The lesion is described as raised or bumpy; the subject is a male aged 30–39; the lesion involves the arm; the patient considered this a rash; the photo was captured at an angle; present for one to three months; the contributor reports itching:
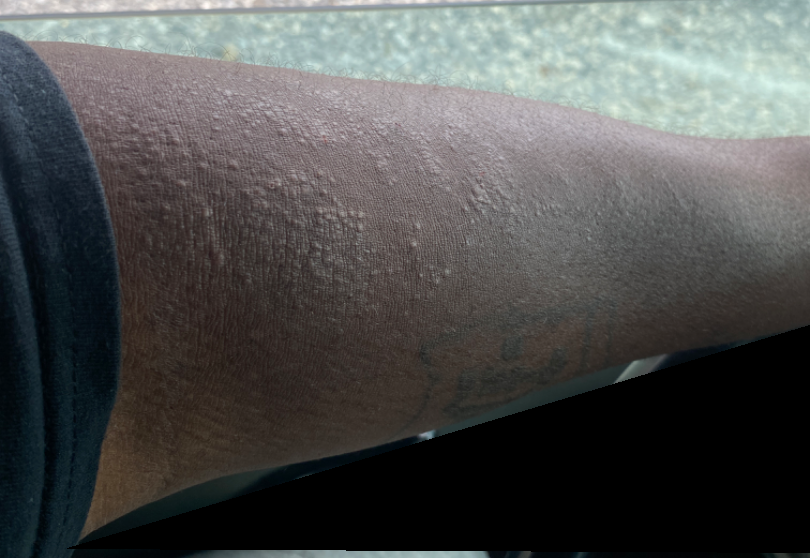On independent review by the dermatologists, the differential, in no particular order, includes Chronic dermatitis, NOS and Amyloidosis of skin; less likely is Lichen Simplex Chronicus; a more distant consideration is Lichen planus/lichenoid eruption; less probable is Eczema.